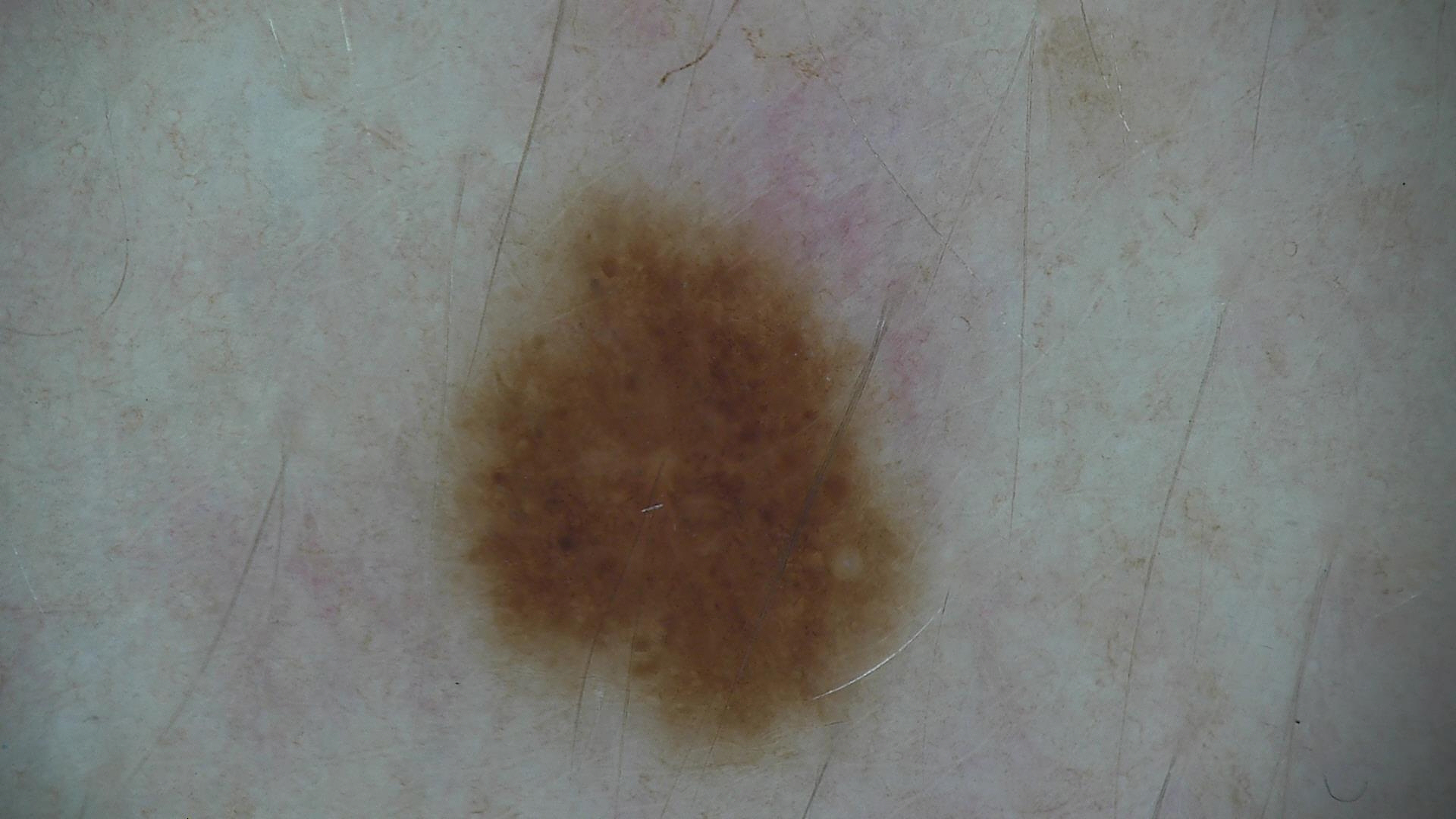Case:
• image — dermatoscopy
• diagnostic label — dysplastic junctional nevus (expert consensus)